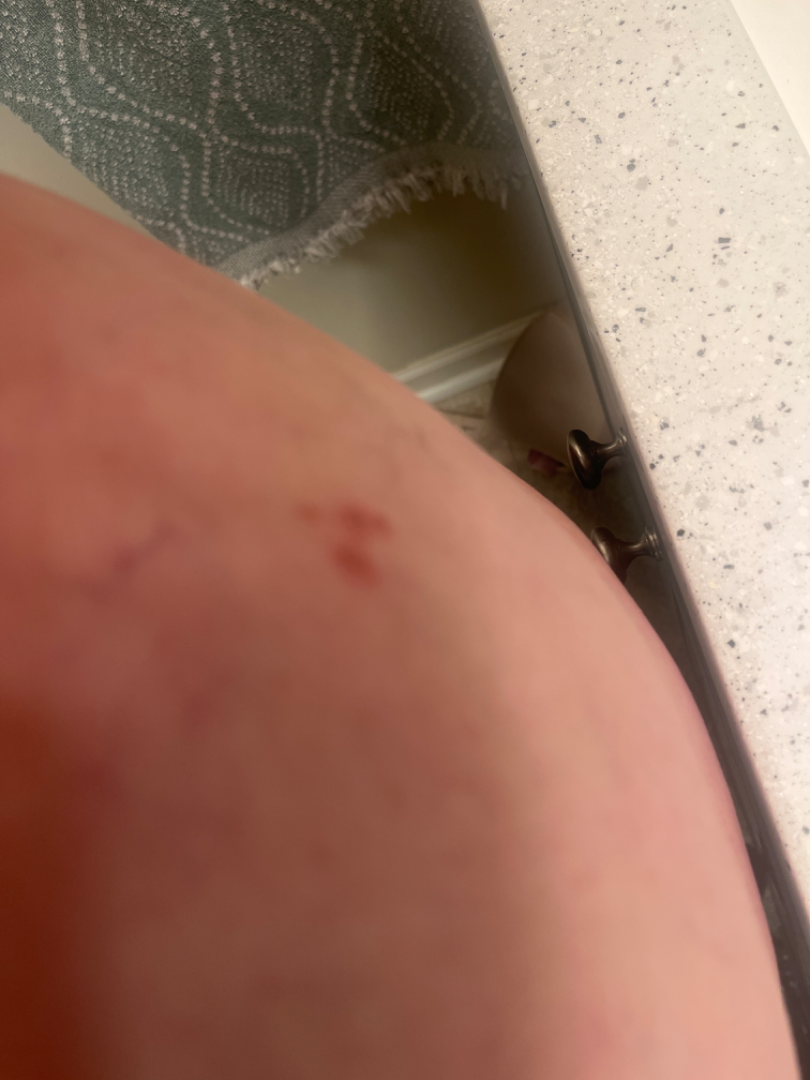{"shot_type": "at an angle", "differential": {"leading": ["Insect Bite"], "considered": ["Impetigo", "Eczema"]}}